Located on the leg, back of the hand, front of the torso, top or side of the foot and arm; an image taken at an angle; male contributor, age 18–29; lay graders estimated 2 on the Monk Skin Tone; reported duration is one to four weeks; the patient described the issue as a rash; symptoms reported: pain, bothersome appearance and itching — 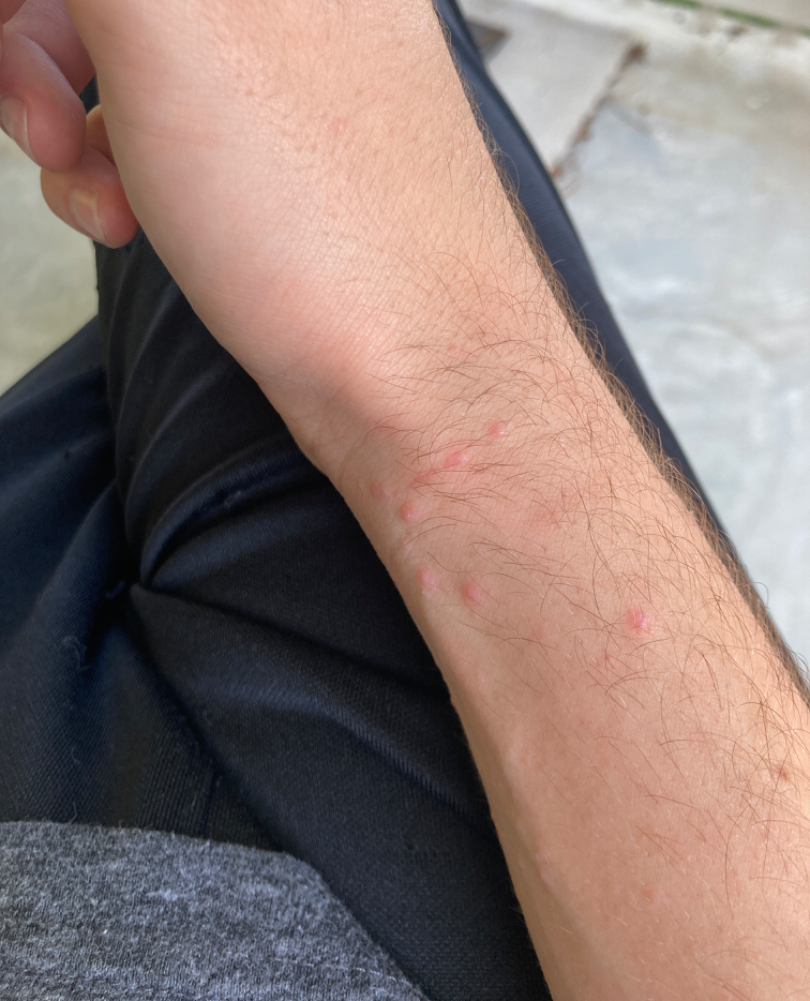Impression: On teledermatology review: Scabies, Insect Bite and Allergic Contact Dermatitis were each considered, in no particular order.